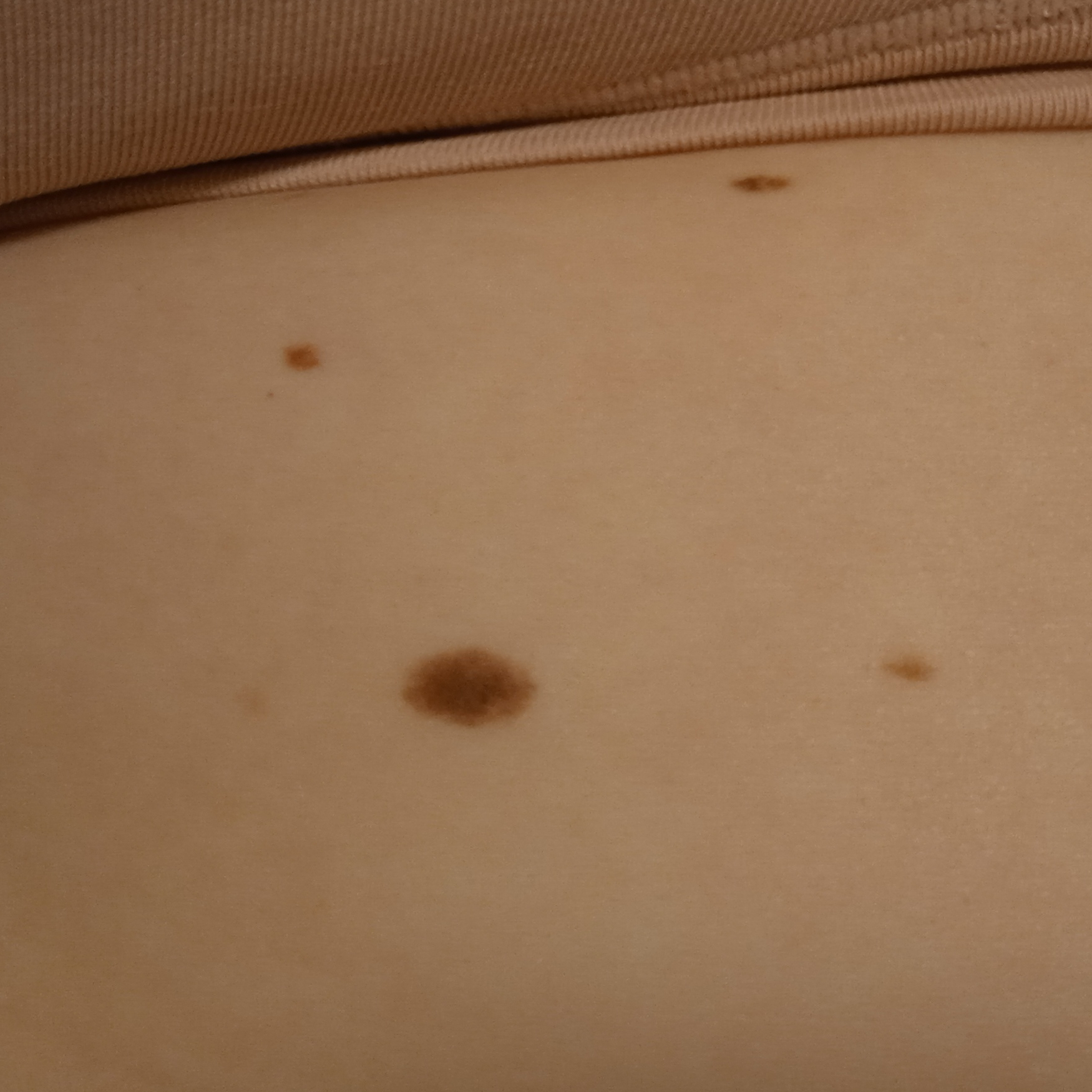image type: clinical photo; sun reaction: skin reddens with sun exposure; nevus count: a moderate number of melanocytic nevi; patient: female, 27 years old; clinical context: research study (no referral diagnosis); body site: the back; diameter: 9.4 mm; diagnostic label: melanocytic nevus (dermatologist consensus).